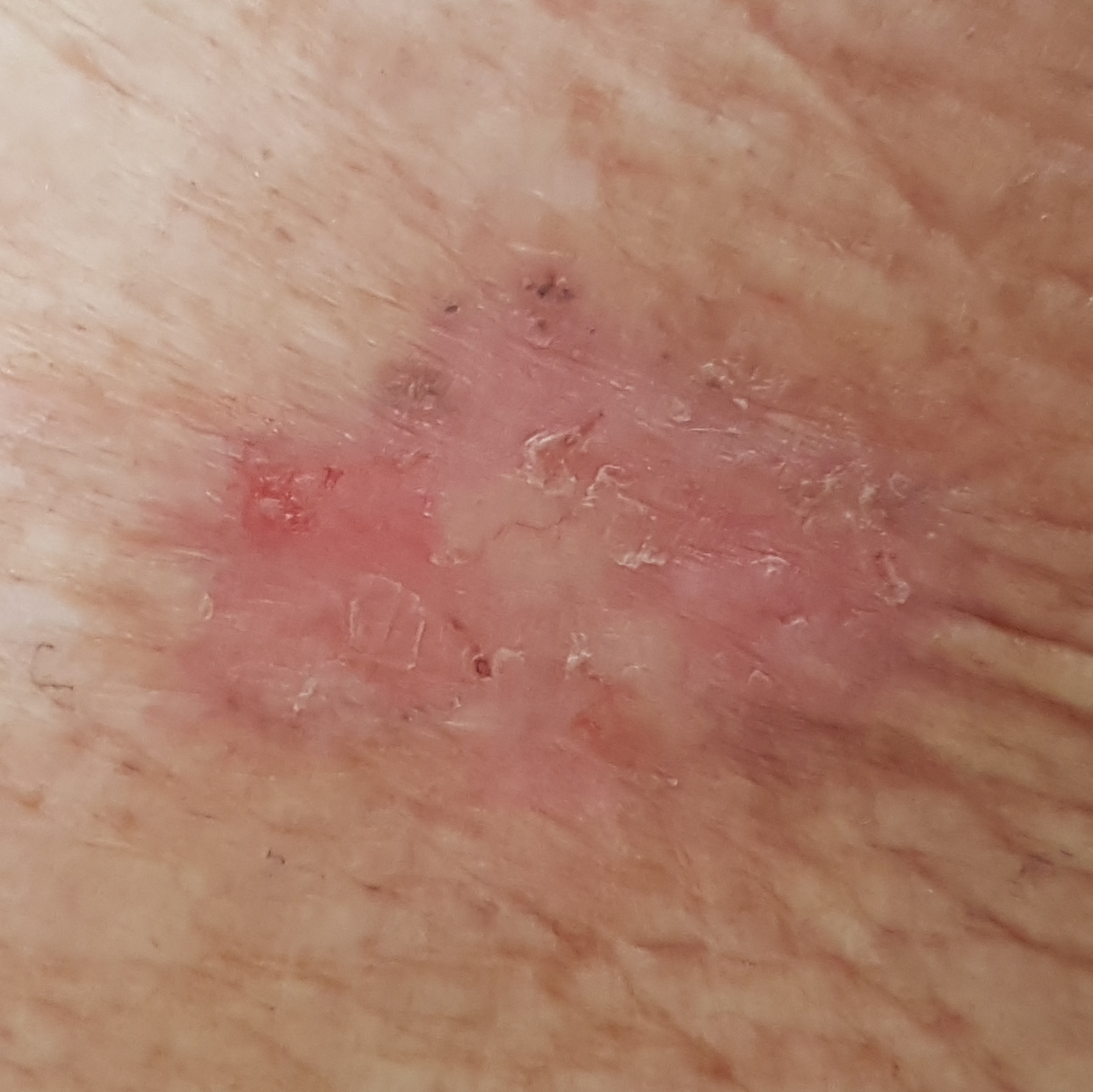Q: Where on the body is the lesion?
A: an arm
Q: What symptoms does the patient report?
A: itching
Q: What is this lesion?
A: basal cell carcinoma (biopsy-proven)